The photograph is a close-up of the affected area · no associated systemic symptoms reported · the contributor is 30–39, male · texture is reported as raised or bumpy · the lesion is associated with enlargement, itching and bothersome appearance · located on the top or side of the foot · the patient considered this a rash · present for one to four weeks:
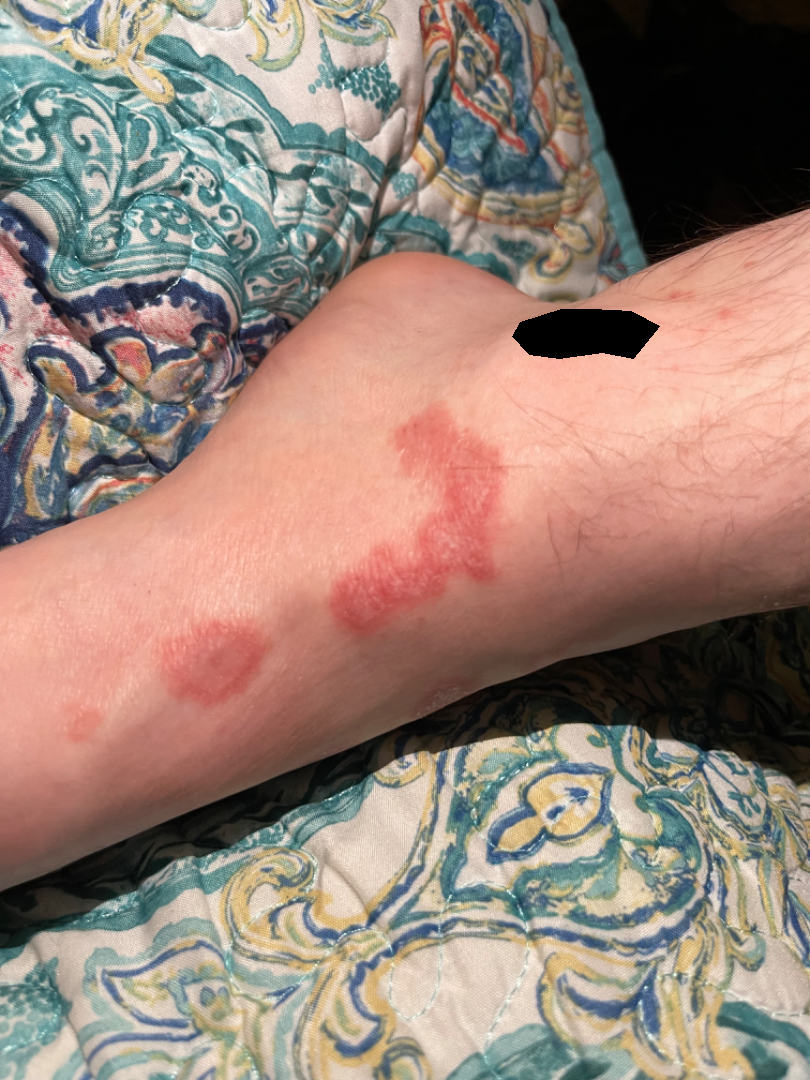The skin condition could not be confidently assessed from this image.